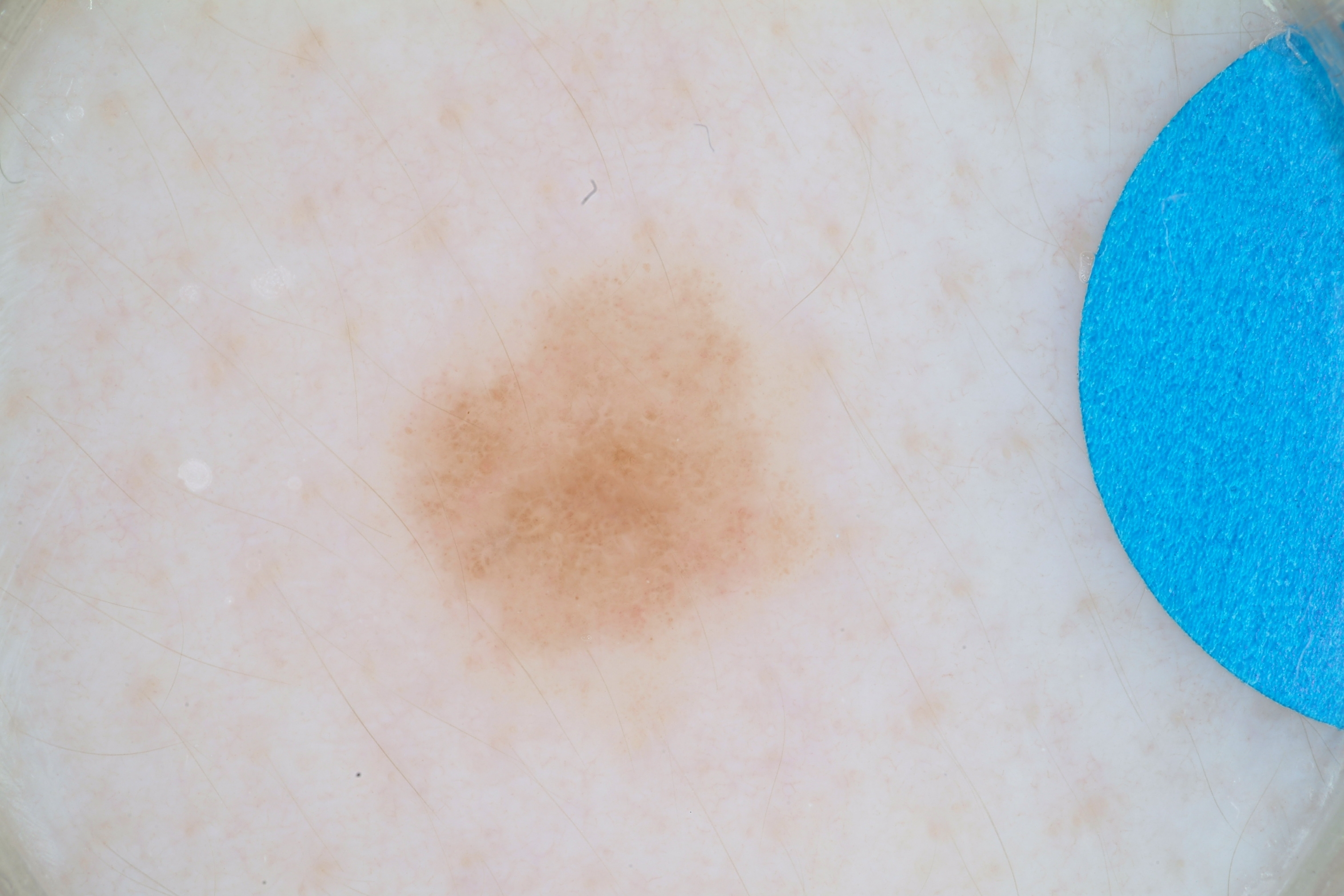A dermatoscopic image of a skin lesion.
Dermoscopic assessment notes globules.
The lesion covers approximately 10% of the dermoscopic field.
With coordinates (x1, y1, x2, y2), lesion location: (392, 267, 818, 676).
Diagnosed as a benign skin lesion.